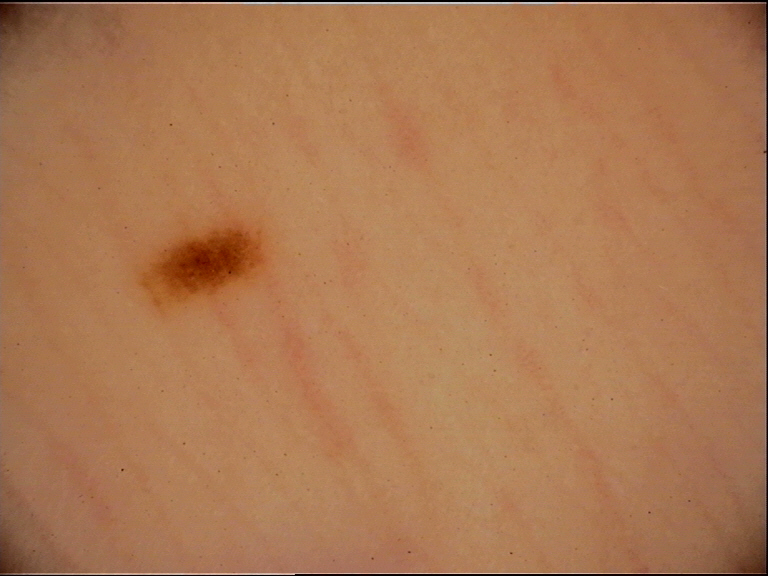lesion_type:
  main_class: banal
  pattern: junctional
diagnosis:
  name: junctional nevus
  code: jb
  malignancy: benign
  super_class: melanocytic
  confirmation: expert consensus